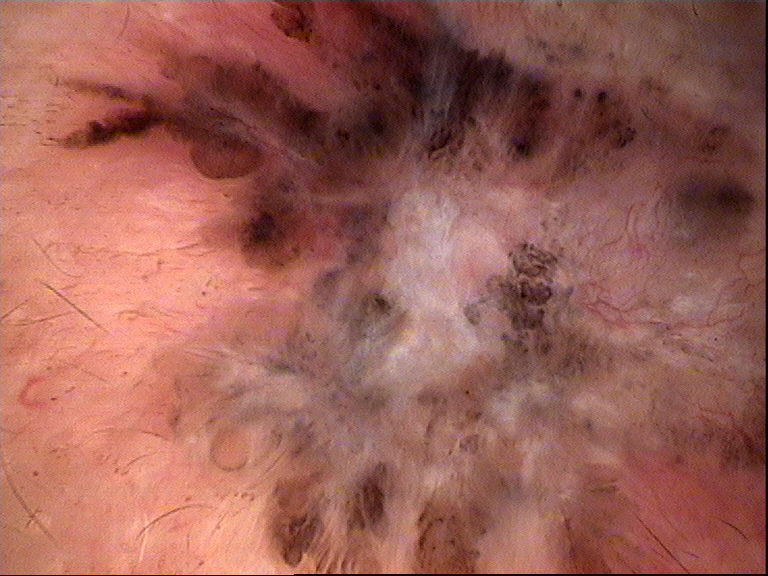Confirmed on histopathology as a basal cell carcinoma.